A dermoscopic image of a skin lesion: 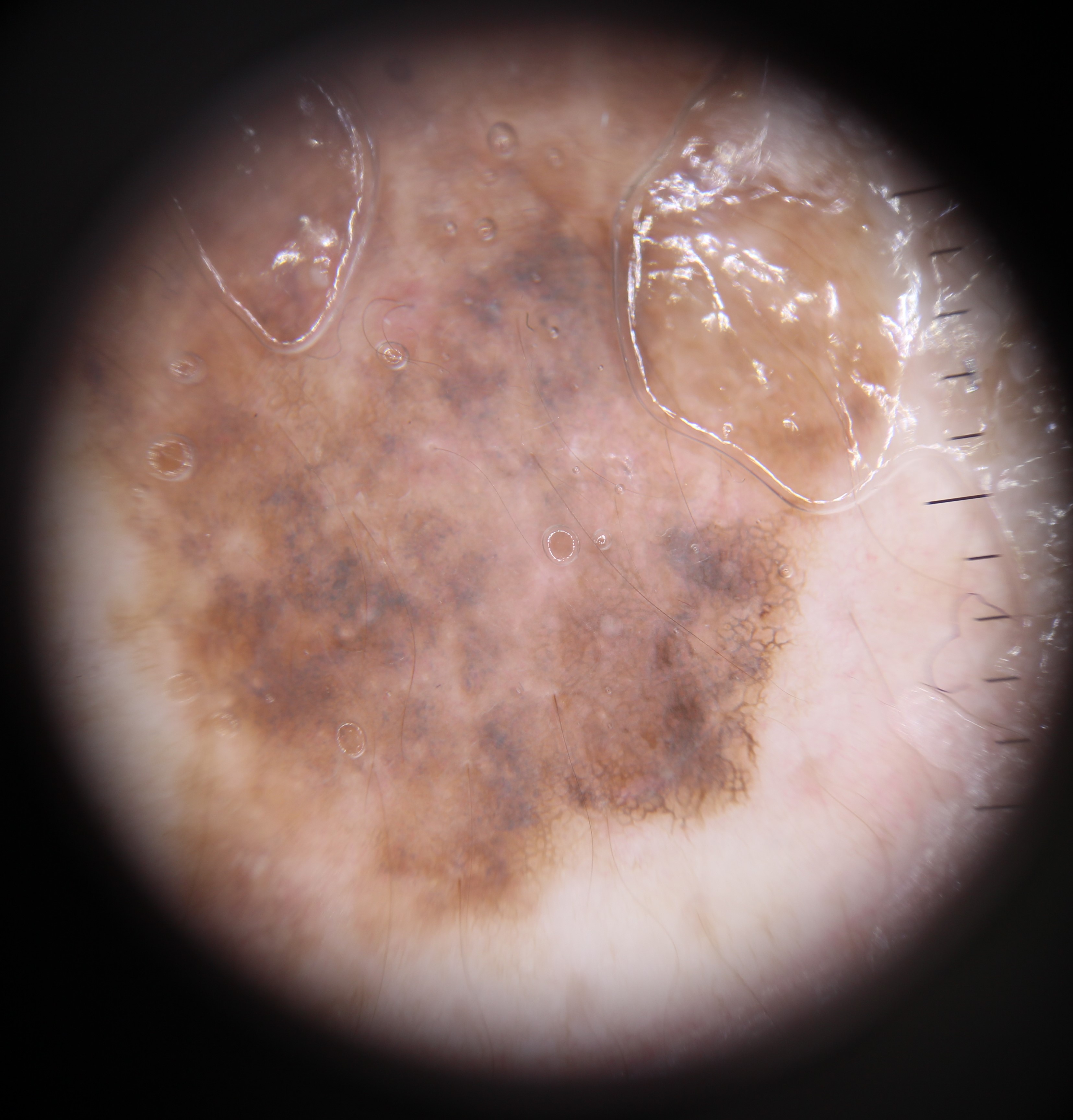Q: What is this lesion?
A: melanoma (biopsy-proven)